A dermoscopic close-up of a skin lesion.
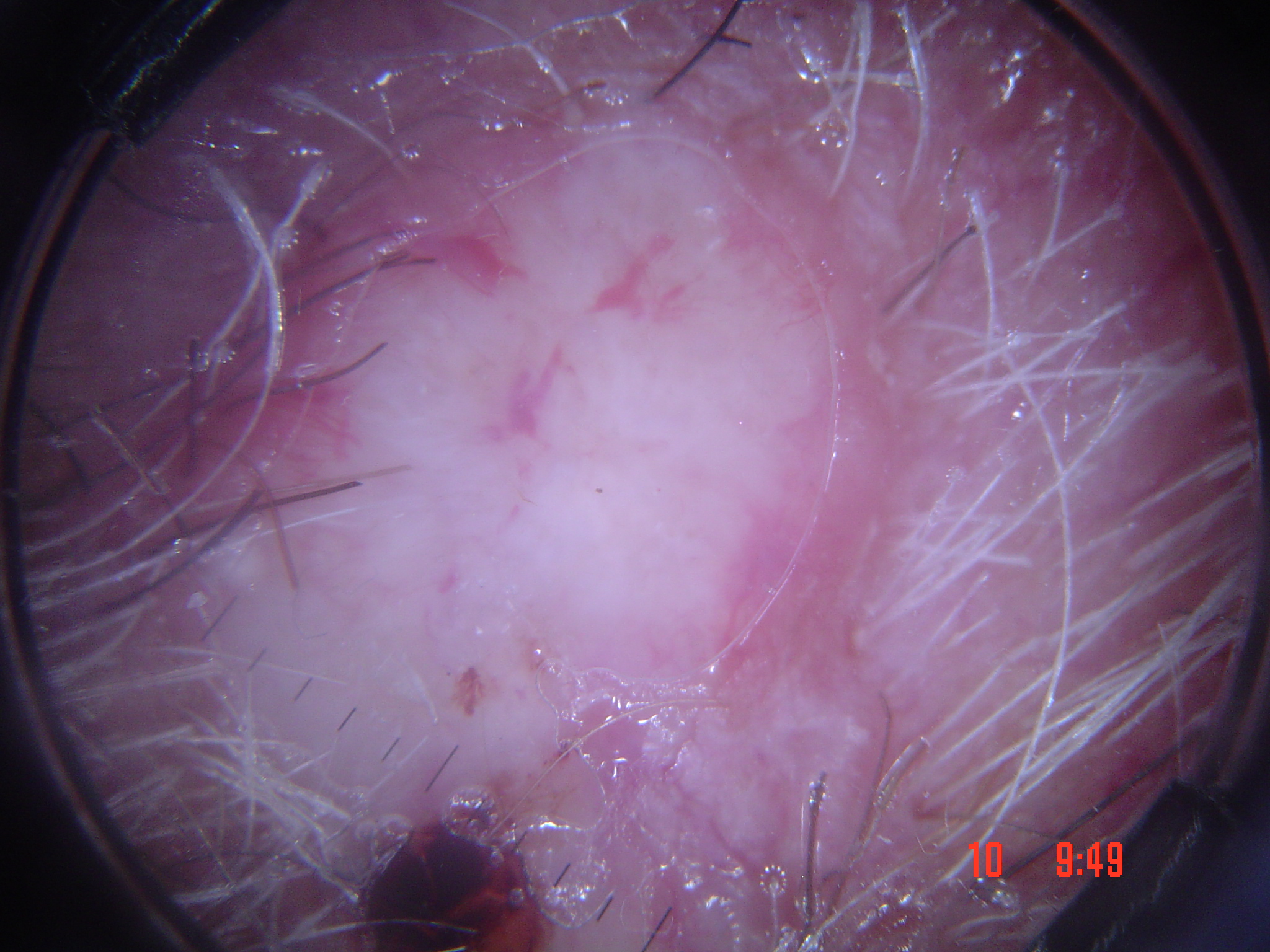Findings:
This is a keratinocytic lesion.
Conclusion:
Confirmed on histopathology as a basal cell carcinoma.